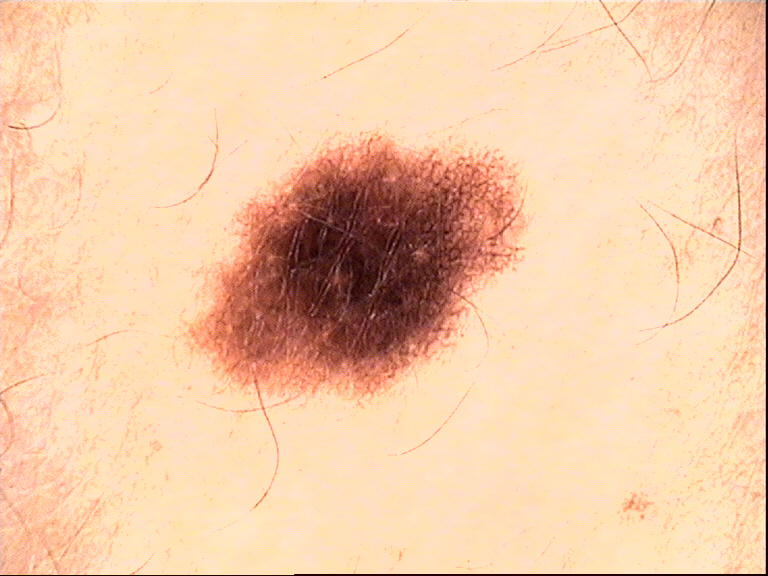Consistent with a dysplastic junctional nevus.